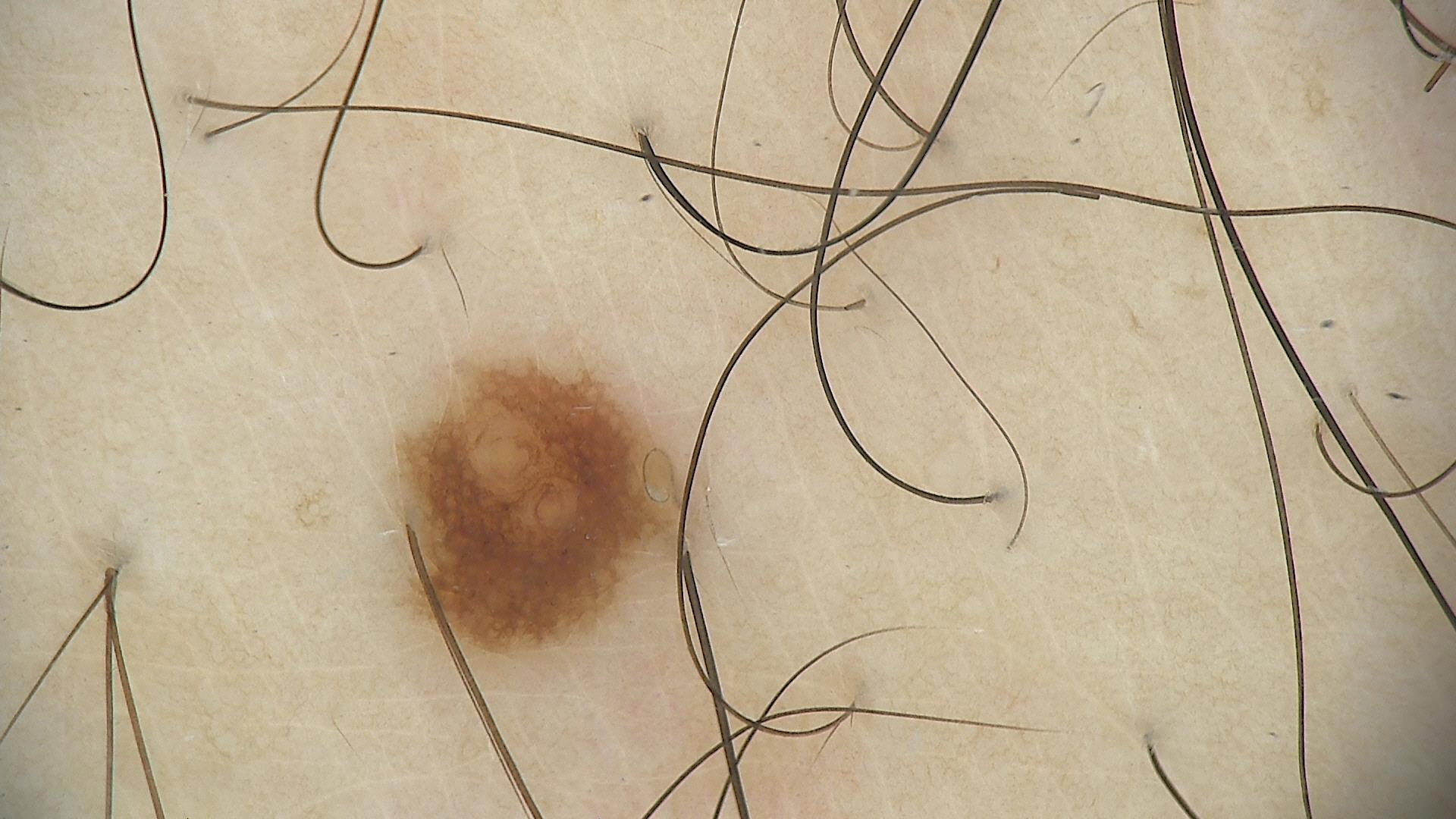Q: What is the diagnosis?
A: dysplastic junctional nevus (expert consensus)